A dermoscopic photograph of a skin lesion:
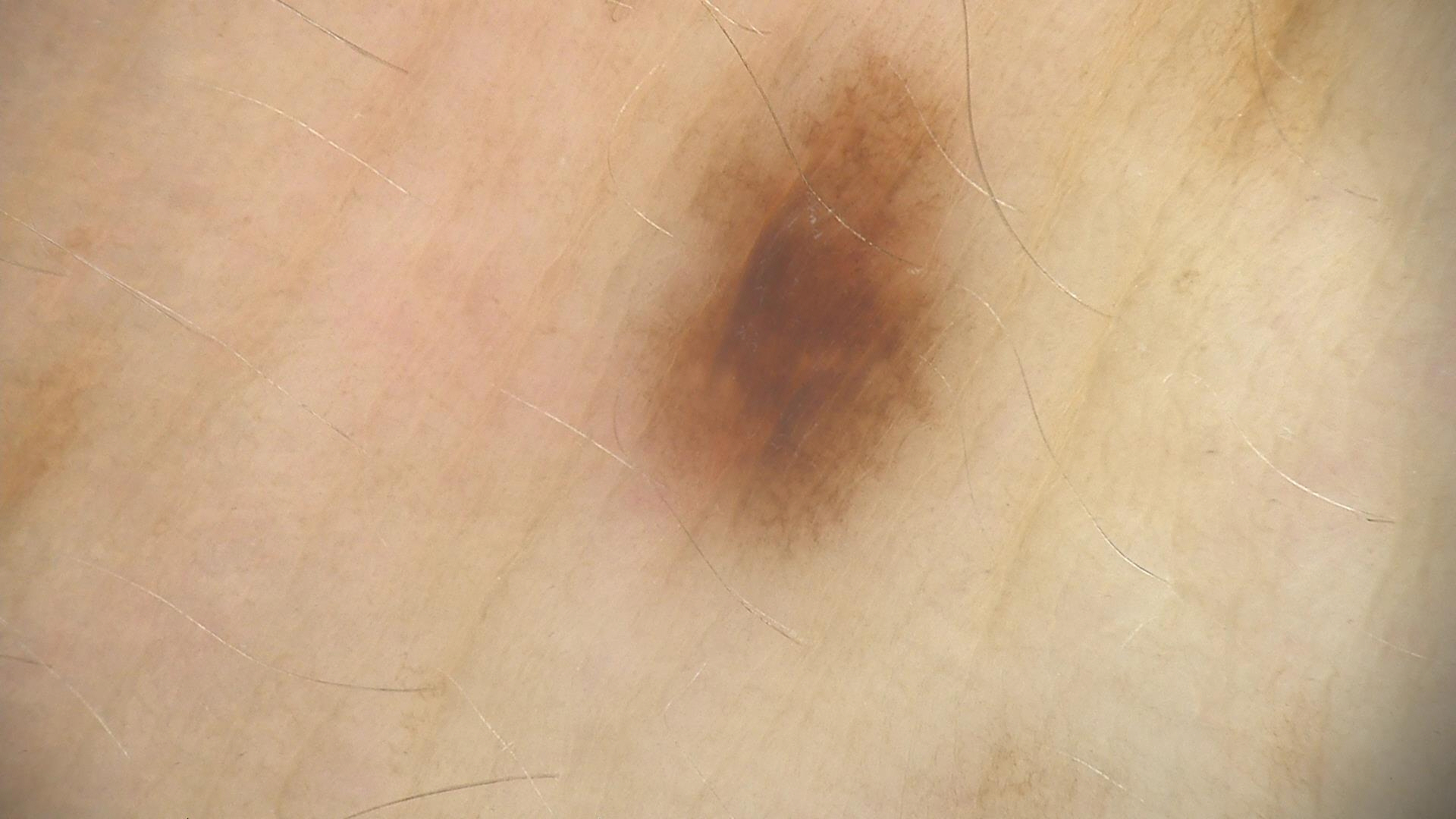Impression: Consistent with a benign lesion — a dysplastic junctional nevus.